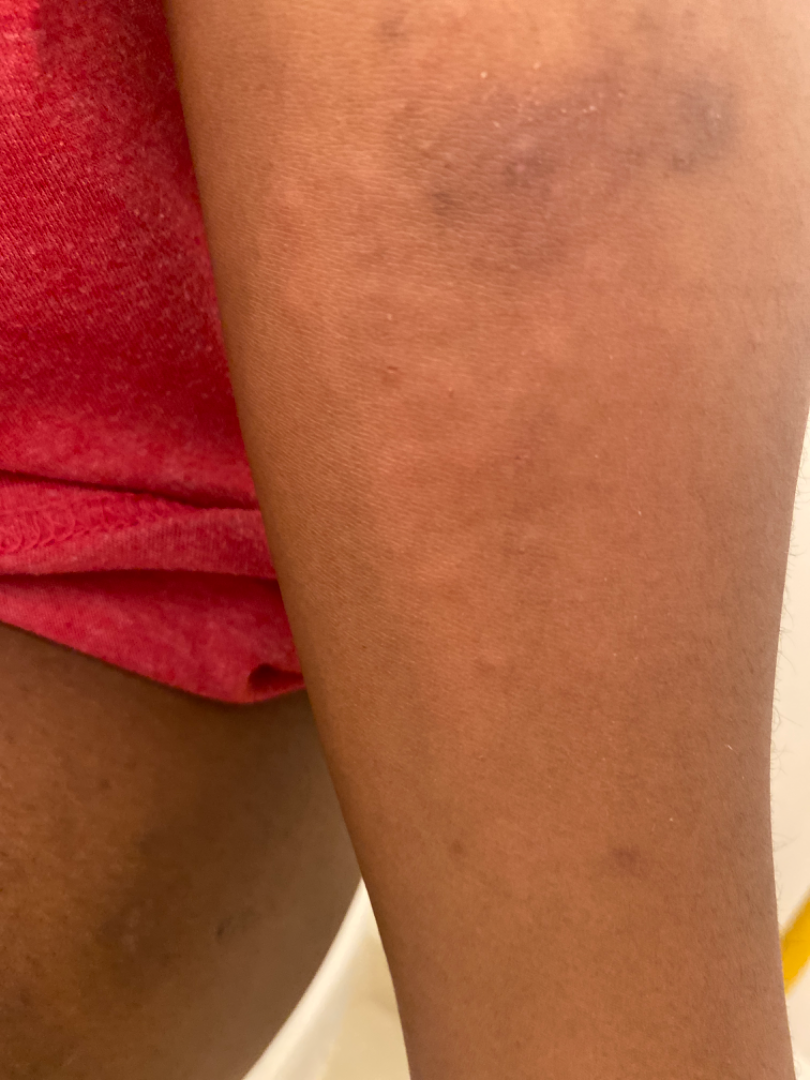differential=most likely Eczema; a more distant consideration is Scabies; less likely is Allergic Contact Dermatitis; less probable is Tinea; lower on the differential is Psoriasis